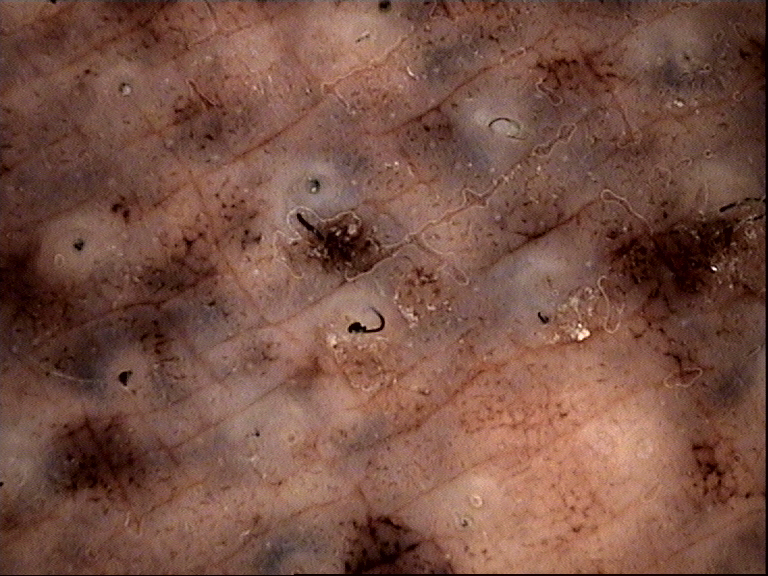  diagnosis:
    name: congenital compound nevus
    code: ccb
    malignancy: benign
    super_class: melanocytic
    confirmation: expert consensus